This is a close-up image. Reported lesion symptoms include bothersome appearance. The patient considered this a rash. Fitzpatrick skin type III; non-clinician graders estimated Monk skin tone scale 3. The front of the torso, back of the hand, arm and leg are involved: 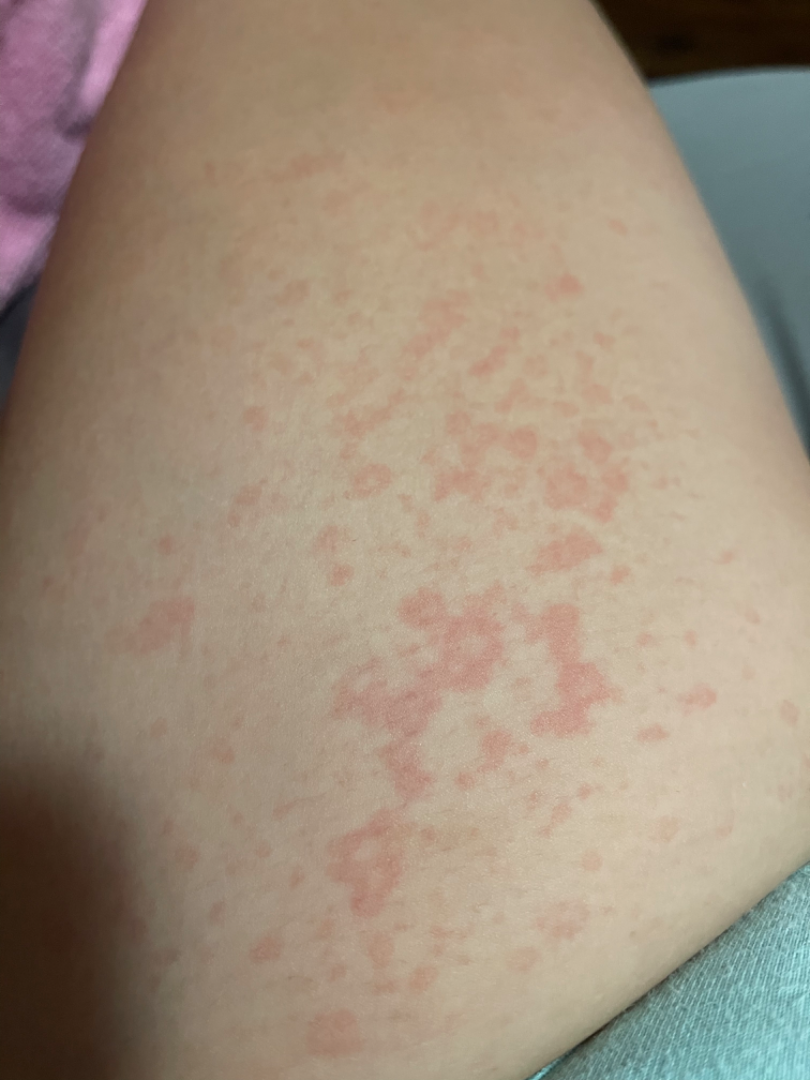differential:
  tied_lead:
    - Drug Rash
    - Viral Exanthem